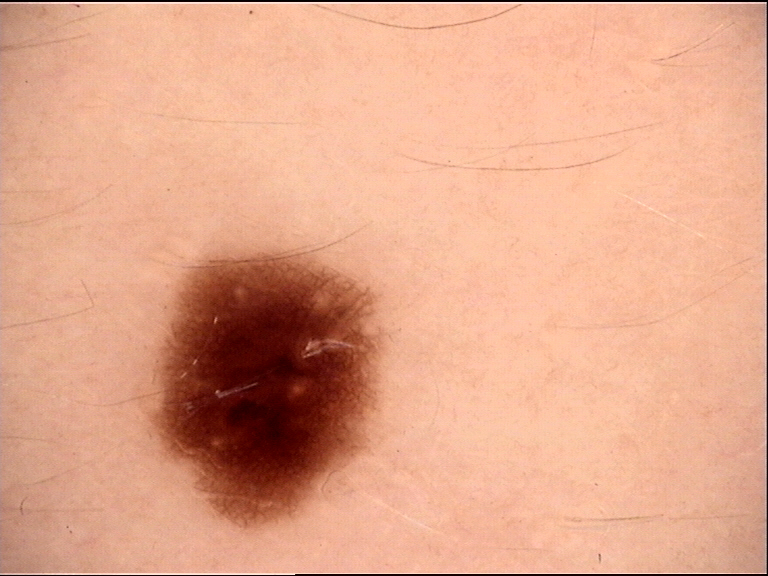image type: dermoscopy
diagnosis: dysplastic junctional nevus (expert consensus)